The photograph is a close-up of the affected area. The patient indicates burning, pain and itching. The patient indicates the lesion is fluid-filled, raised or bumpy and rough or flaky. The back of the torso is involved. The subject is female. Present for less than one week:
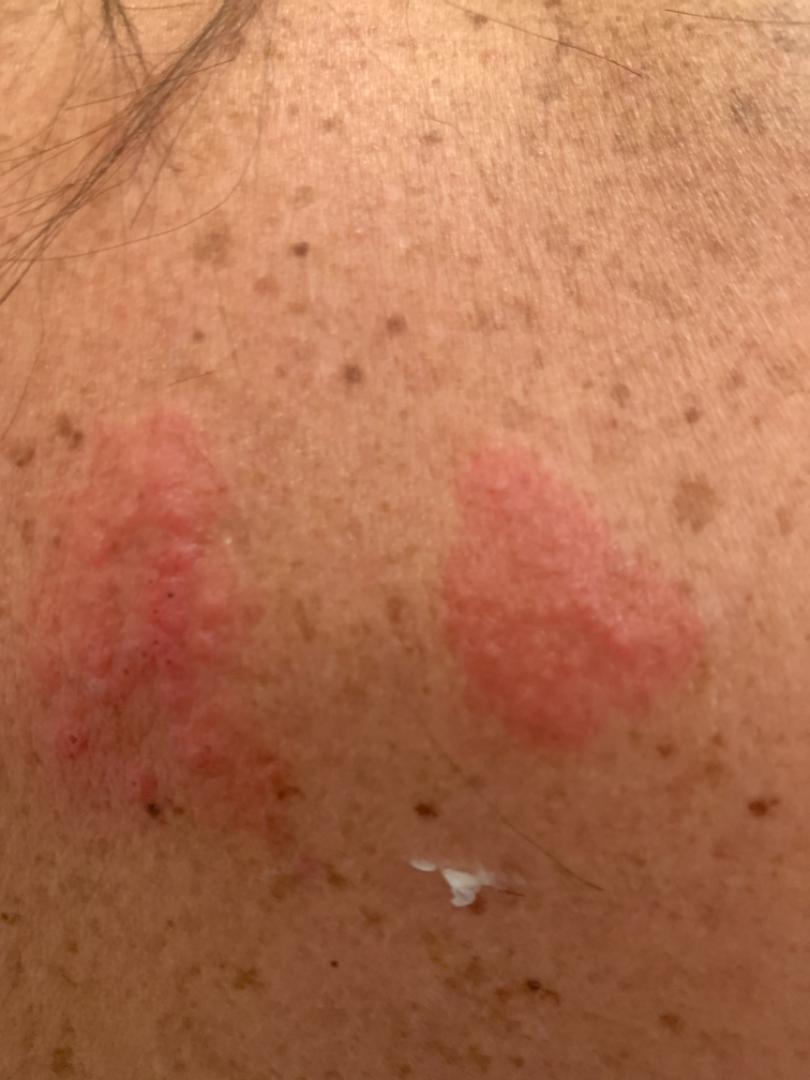{"differential": {"Herpes Zoster": 0.58, "Contact dermatitis": 0.25, "Allergic Contact Dermatitis": 0.17}}